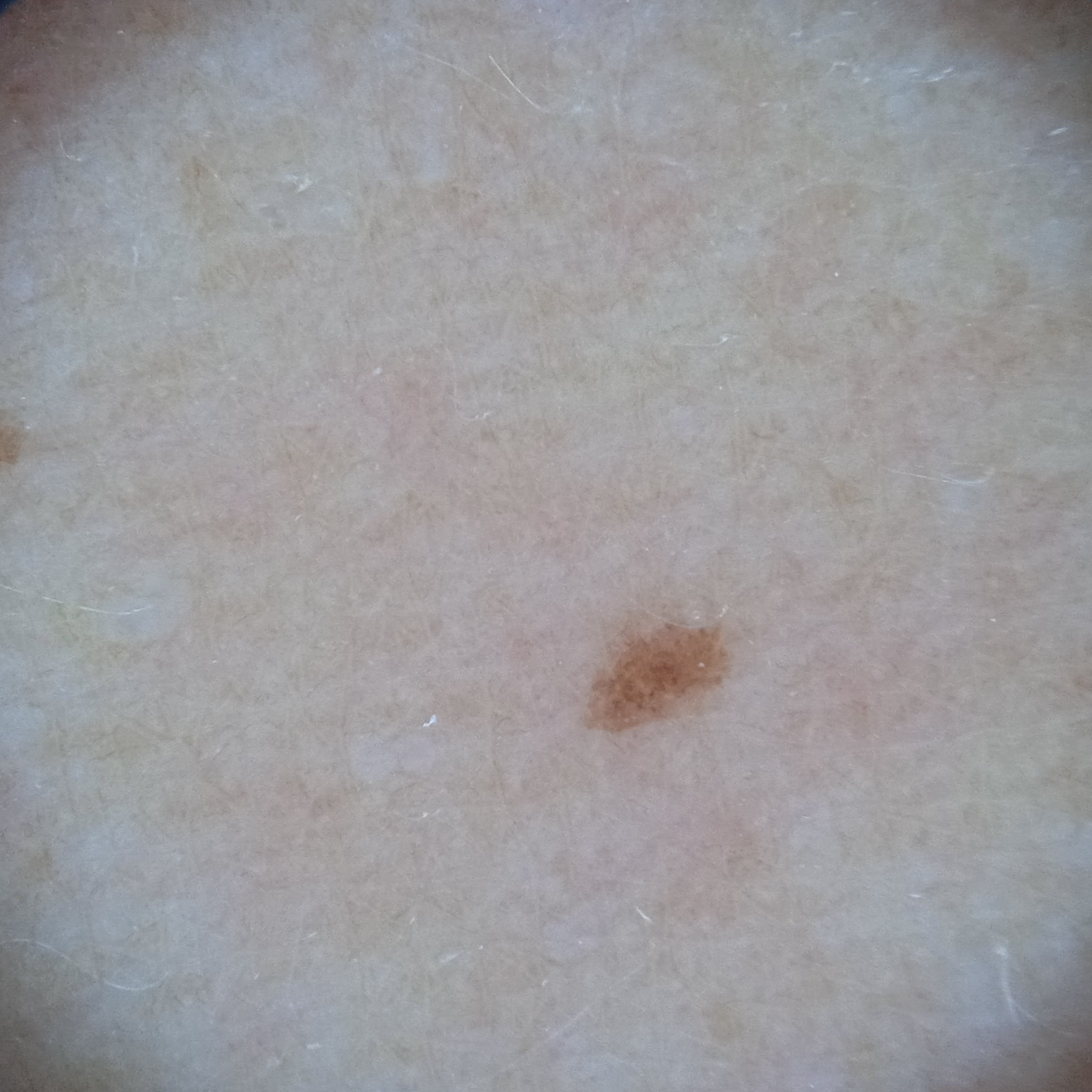<record>
<referral>research study (no referral diagnosis)</referral>
<image>dermoscopy</image>
<patient>
<age>58</age>
<sex>female</sex>
</patient>
<mole_burden>a moderate number of melanocytic nevi</mole_burden>
<lesion_location>an arm</lesion_location>
<diagnosis>
<name>melanocytic nevus</name>
<malignancy>benign</malignancy>
</diagnosis>
</record>